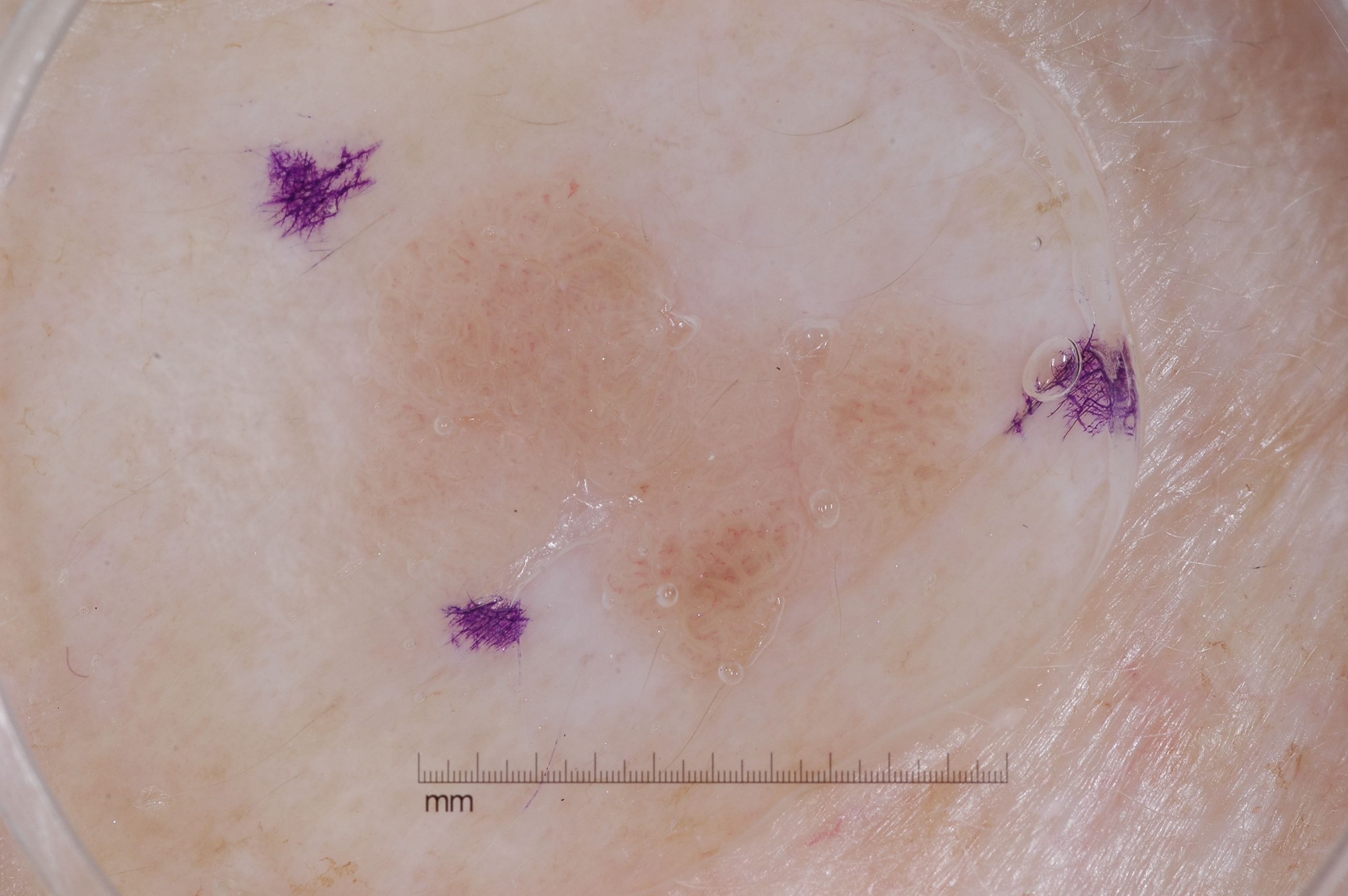Q: Who is the patient?
A: female, roughly 75 years of age
Q: What kind of image is this?
A: dermoscopic image
Q: Where is the lesion located?
A: <bbox>323, 168, 1029, 716</bbox>
Q: Which assessed dermoscopic features were absent?
A: milia-like cysts, streaks, pigment network, and negative network
Q: What is this lesion?
A: a seborrheic keratosis, a benign lesion